A dermoscopic image of a skin lesion: 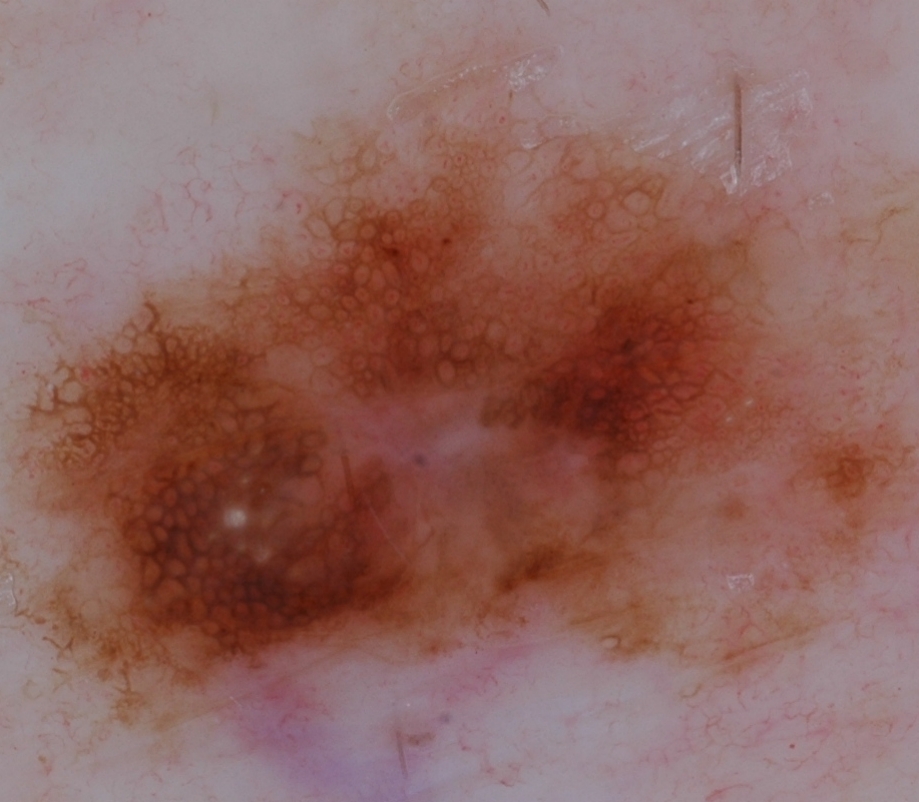Dermoscopy demonstrates globules, milia-like cysts, and pigment network. The lesion reaches across nearly the entire image. Diagnosed as a melanocytic nevus.